A female subject, aged 58 to 62; a dermoscopic view of a skin lesion — 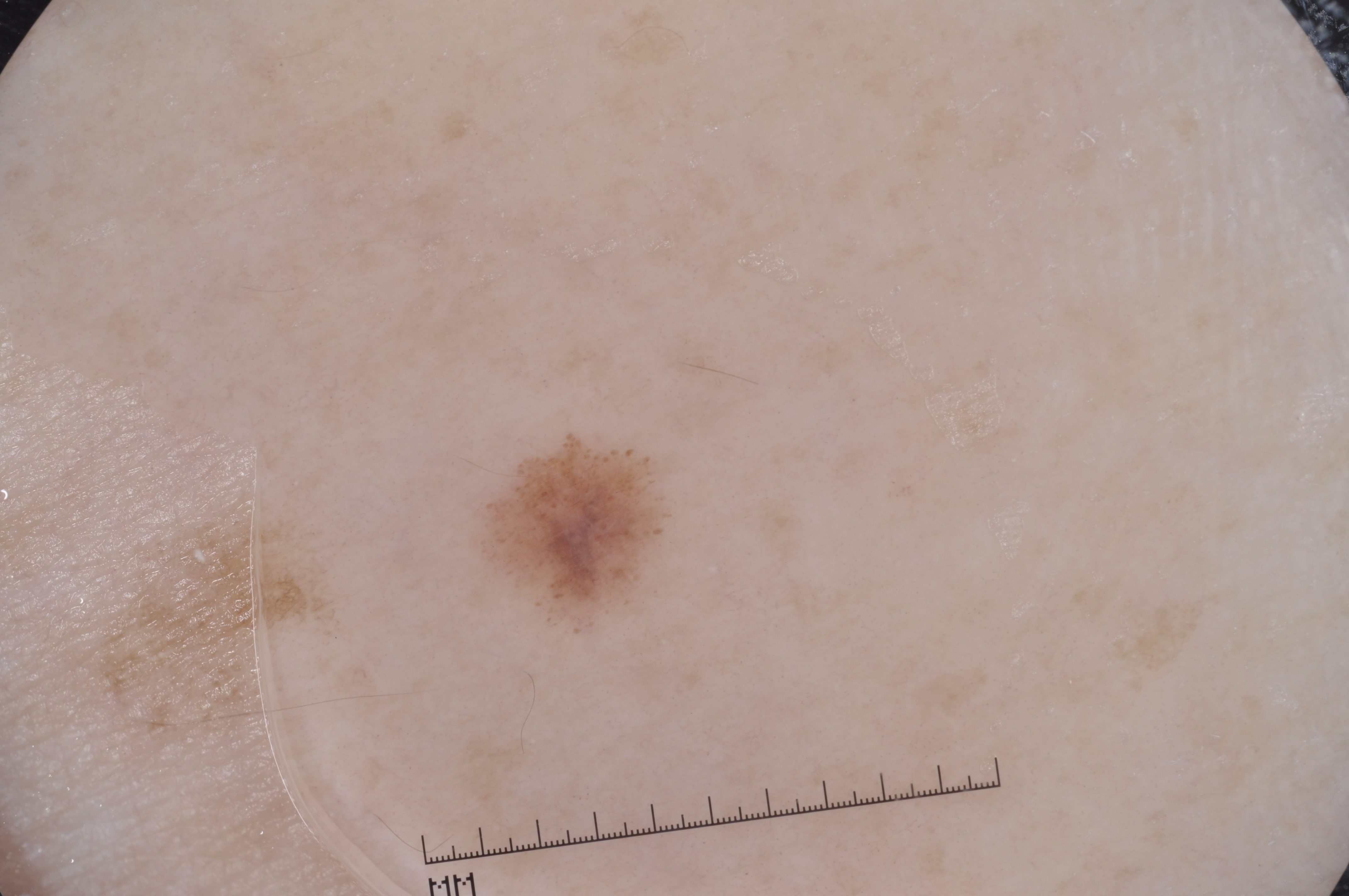– dermoscopic features assessed but absent — milia-like cysts, pigment network, streaks, and negative network
– lesion bbox — [495, 441, 664, 609]
– diagnostic label — a melanocytic nevus, a benign skin lesion